A skin lesion imaged with a dermatoscope.
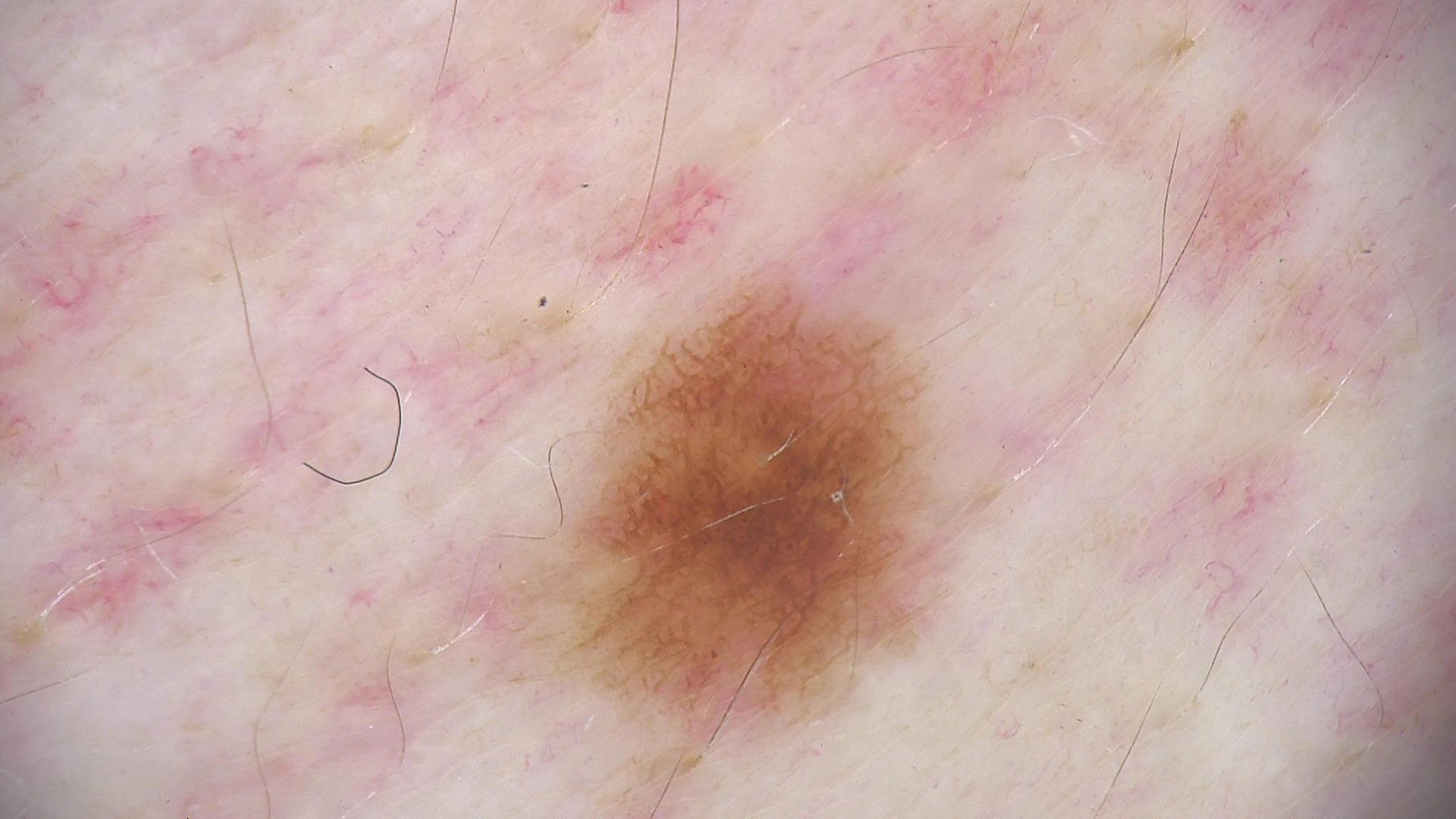Labeled as a dysplastic junctional nevus.